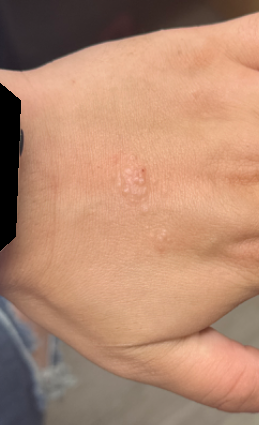{
  "differential": "Contact dermatitis"
}